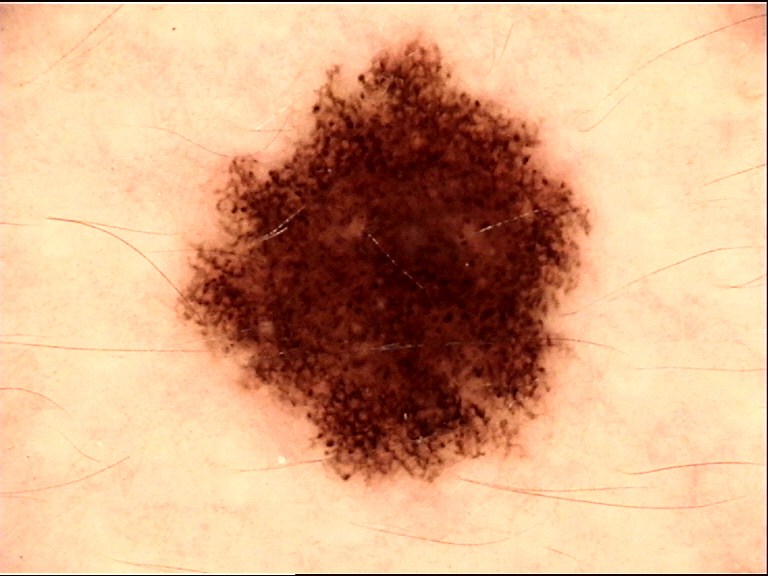Diagnosed as a dysplastic compound nevus.